Close-up view.
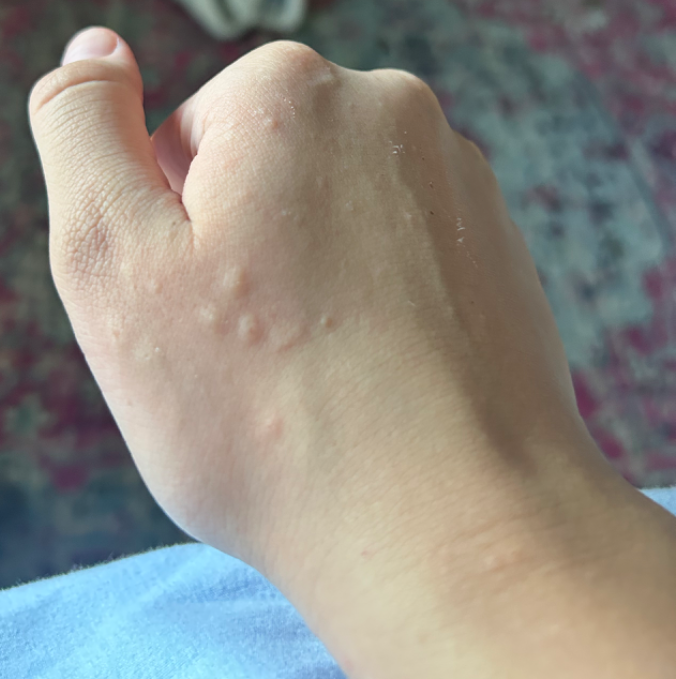Favoring Molluscum Contagiosum; an alternative is Granuloma annulare; less likely is Keratoderma.